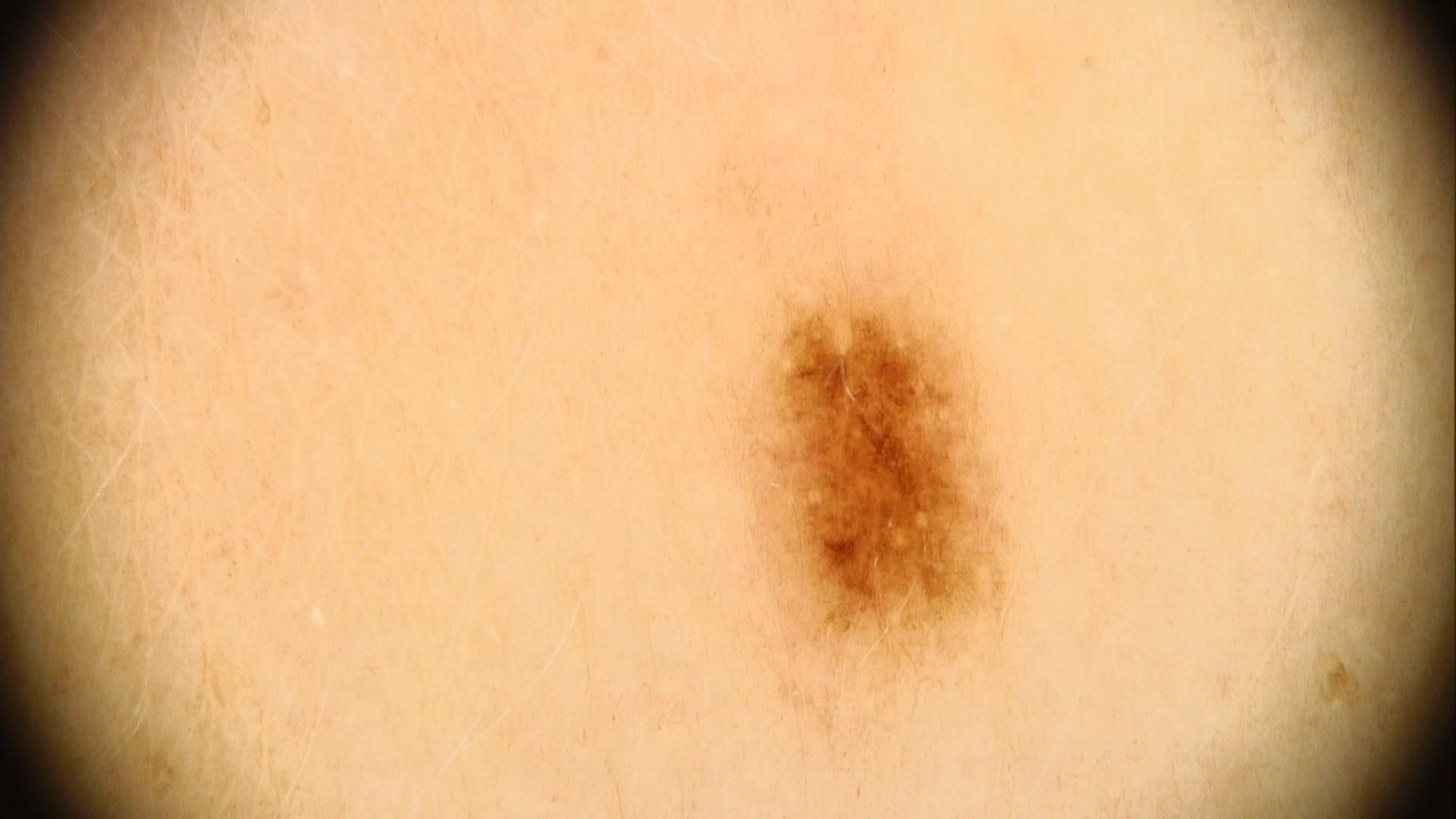The clinical assessment was a nevus.